The lesion is associated with itching and bothersome appearance. The patient considered this a rash. This image was taken at a distance. Located on the leg. The contributor is a female aged 30–39. Skin tone: Fitzpatrick IV; non-clinician graders estimated Monk skin tone scale 4–5:
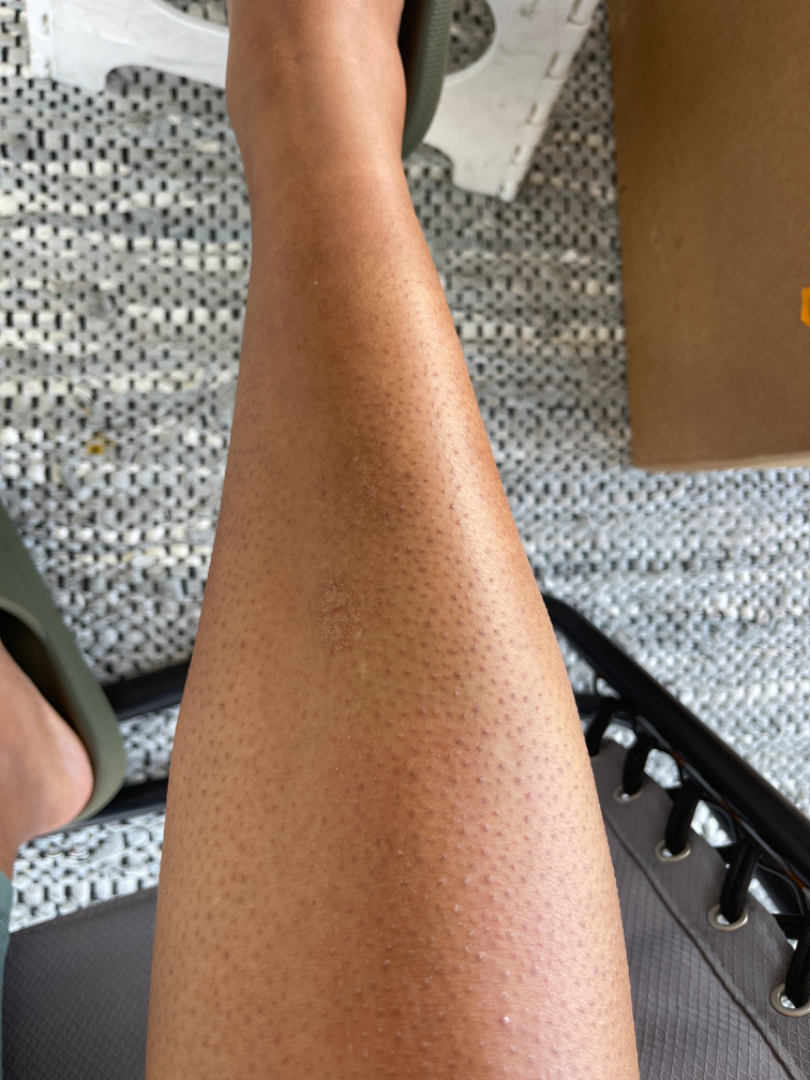{
  "differential": {
    "leading": [
      "Verruca vulgaris"
    ],
    "considered": [
      "SK/ISK"
    ]
  }
}